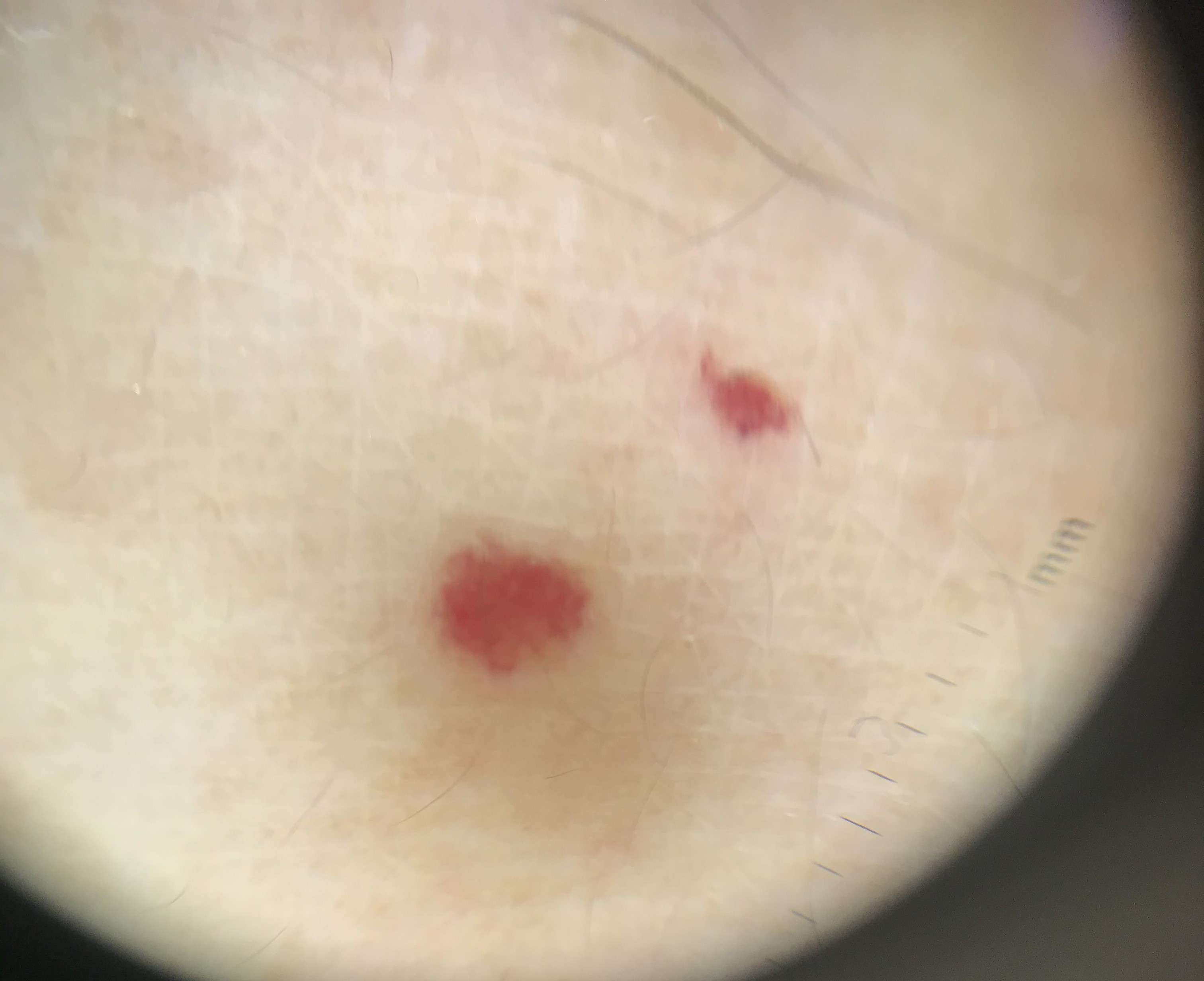A dermoscopic close-up of a skin lesion. The diagnostic label was a vascular lesion — a hemangioma.